A dermoscopic image of a skin lesion.
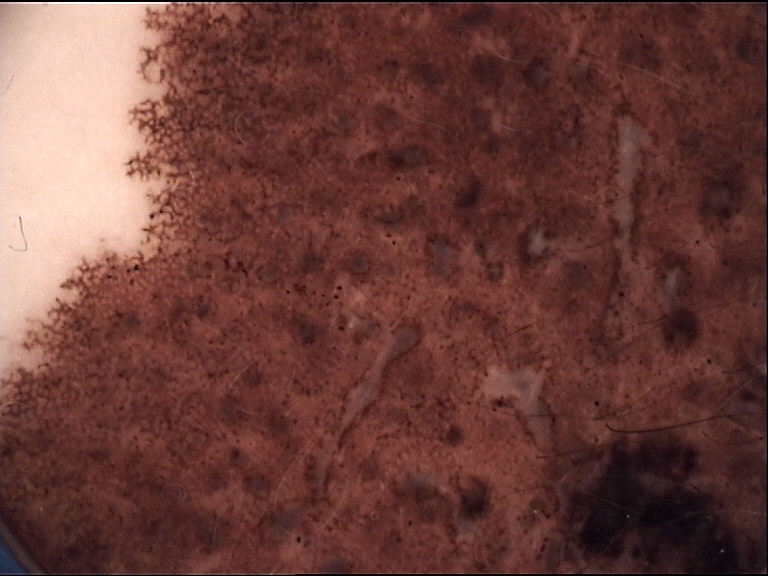lesion type=banal
diagnostic label=congenital compound nevus (expert consensus)